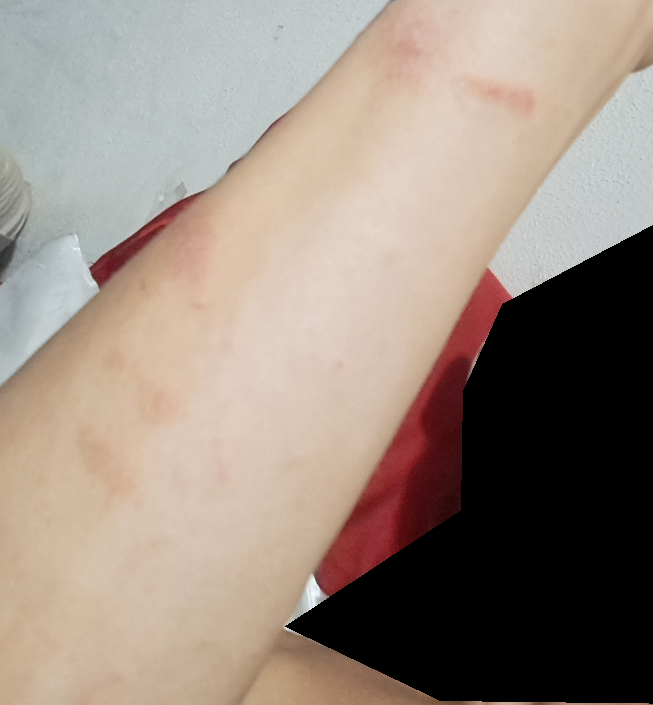assessment — indeterminate